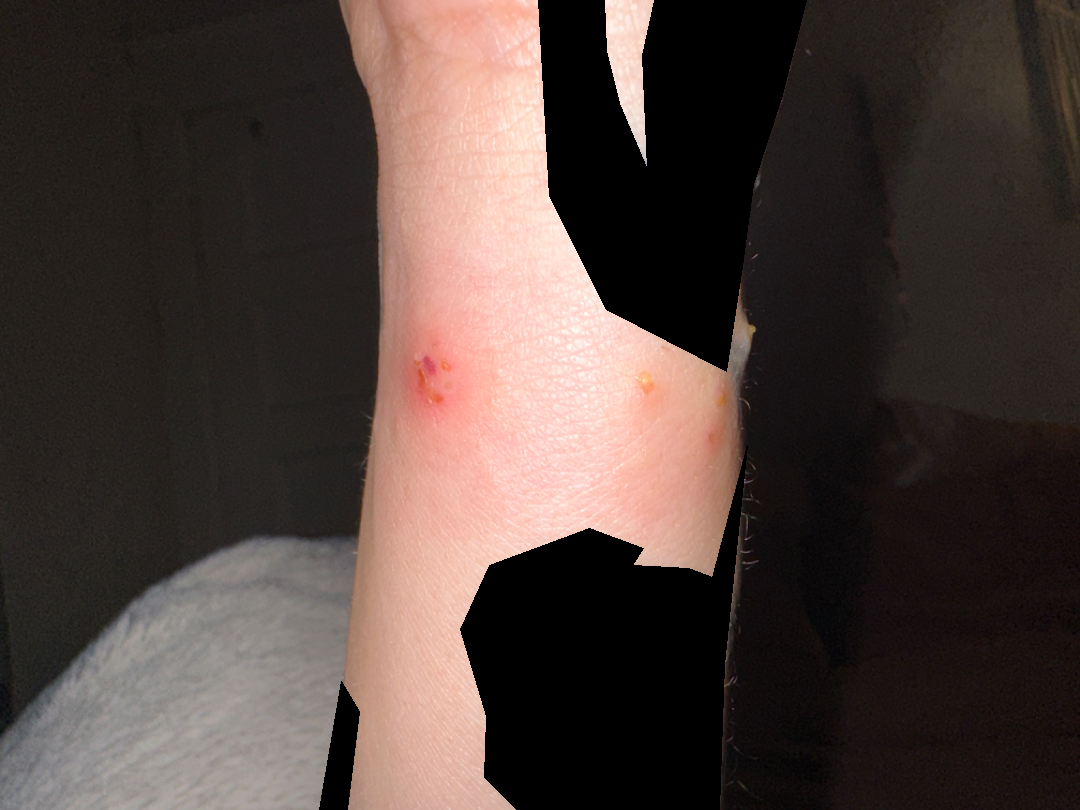The photograph was taken at an angle. Female patient, age 30–39. Located on the arm. On remote dermatologist review, the differential is split between Insect Bite and Impetigo; less probable is Contact dermatitis; less likely is Herpes Simplex; a more distant consideration is Acute dermatitis, NOS; lower on the differential is Allergic Contact Dermatitis.